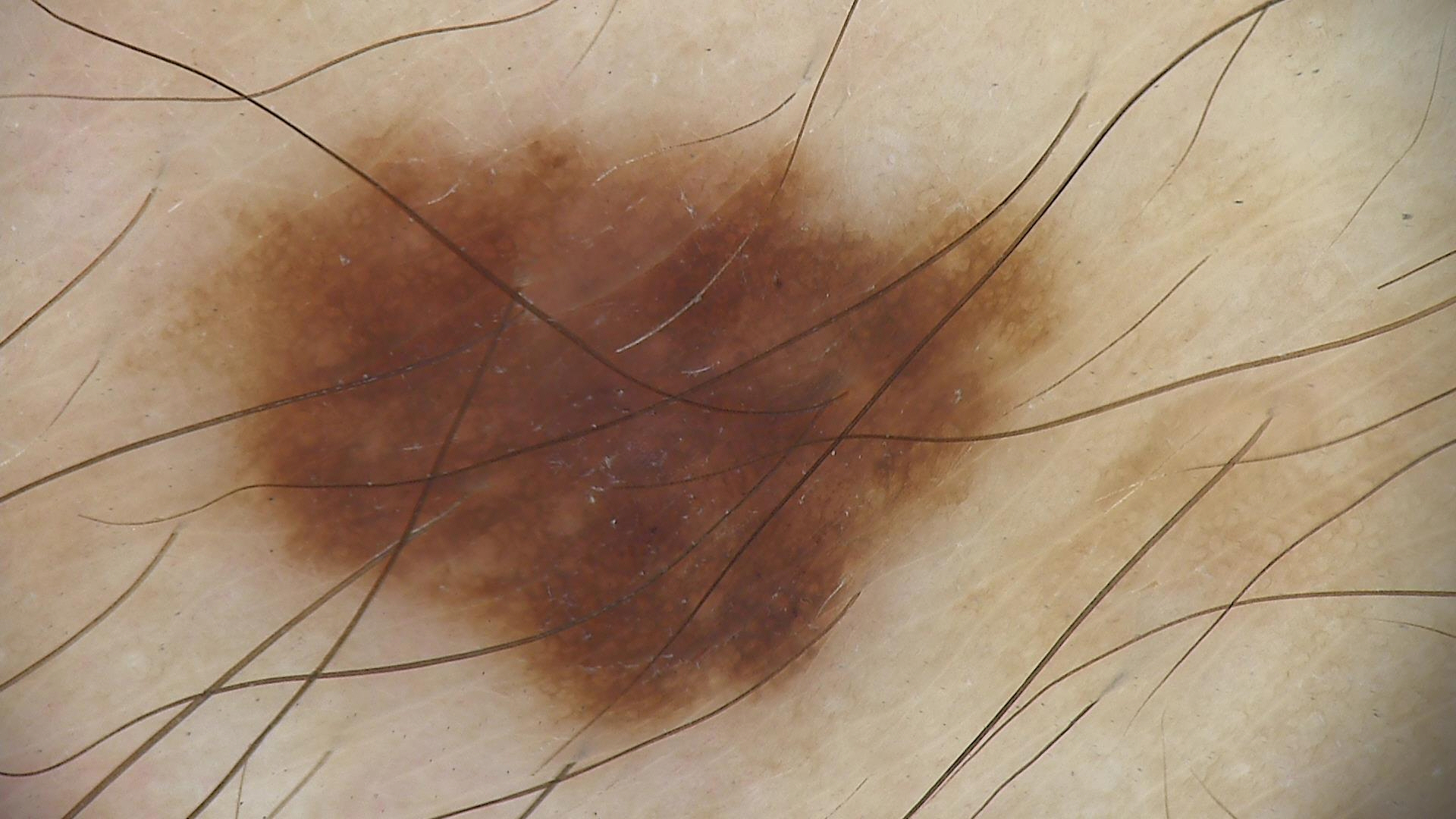image=dermatoscopy
subtype=banal
diagnostic label=junctional nevus (expert consensus)